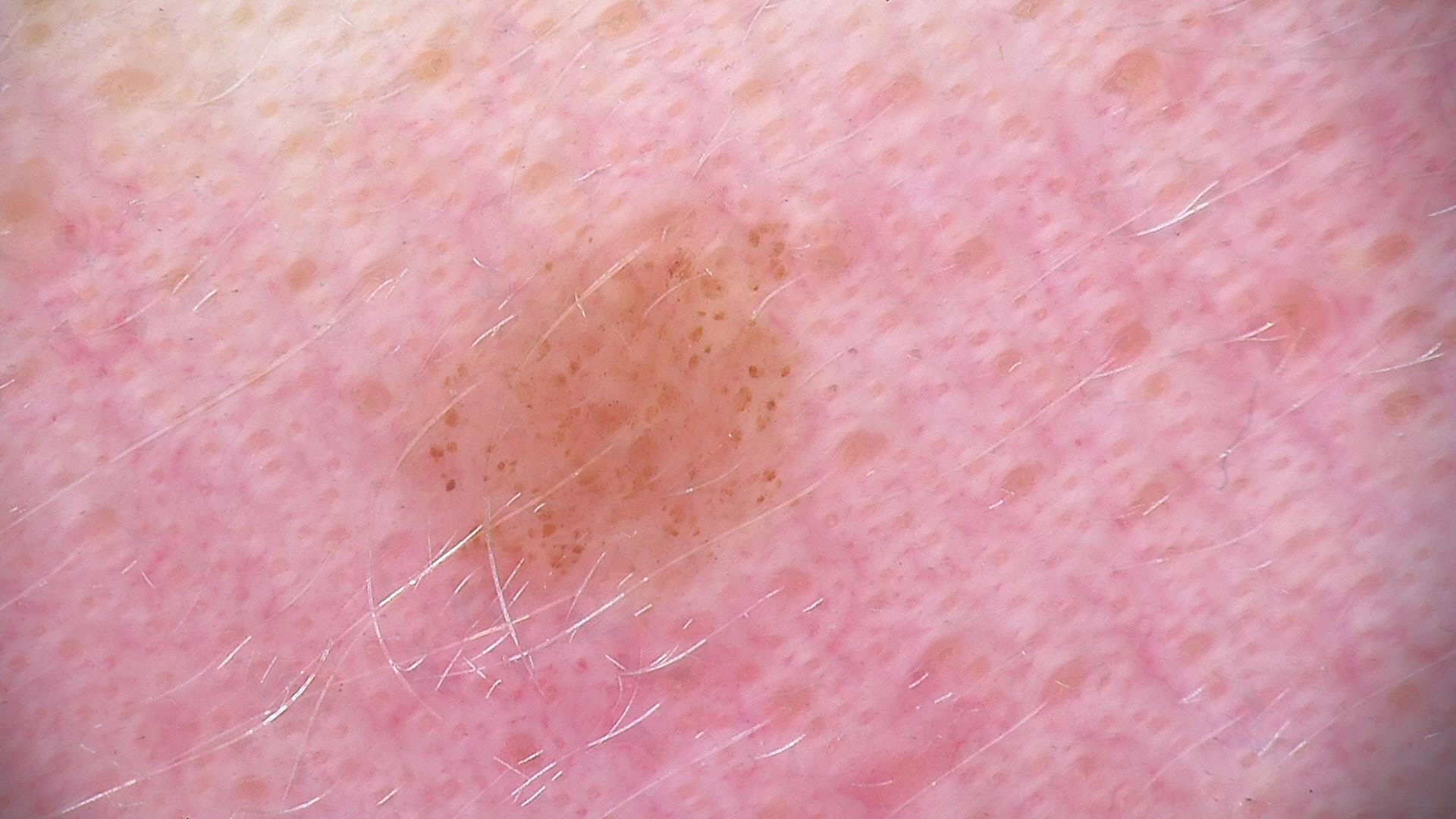classification=banal; class=junctional nevus (expert consensus).